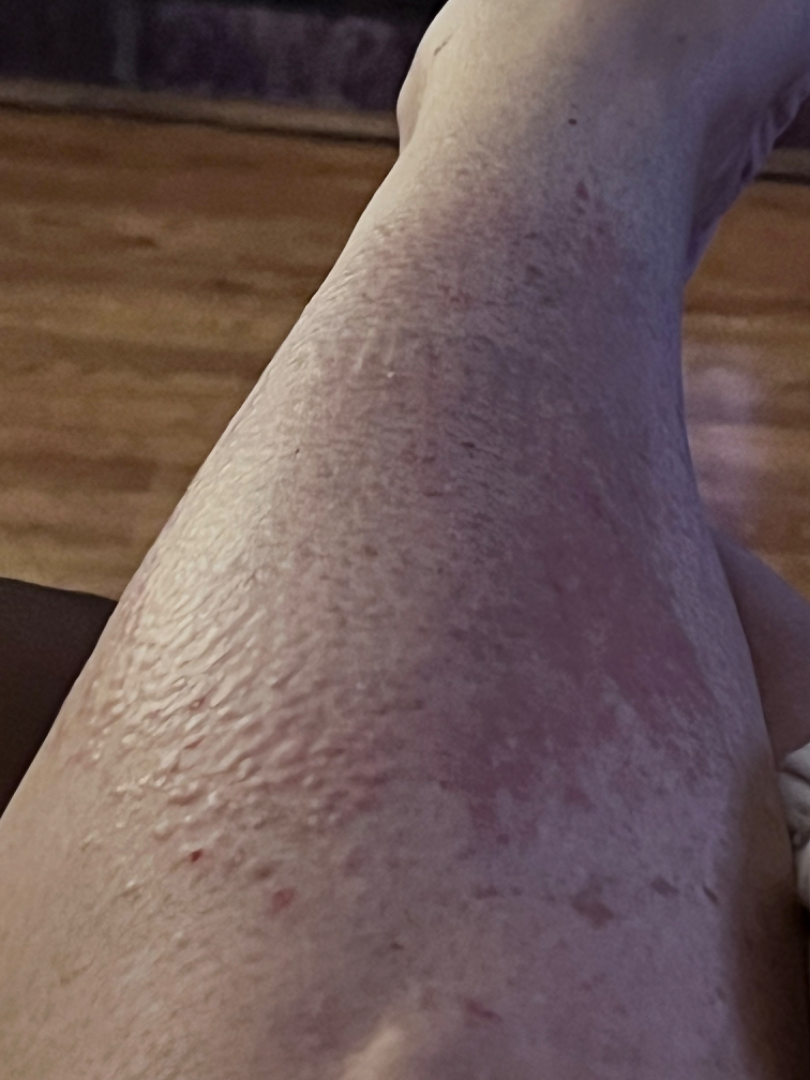view = close-up
patient's own categorization = a rash
subject = female, age 50–59
constitutional symptoms = fatigue and joint pain
site = leg
surface texture = raised or bumpy
impression = reviewed remotely by one dermatologist: most likely Allergic Contact Dermatitis; also raised was Amyloidosis of skin; also on the differential is Pretibial myxedema